This image was taken at an angle · the arm and leg are involved:
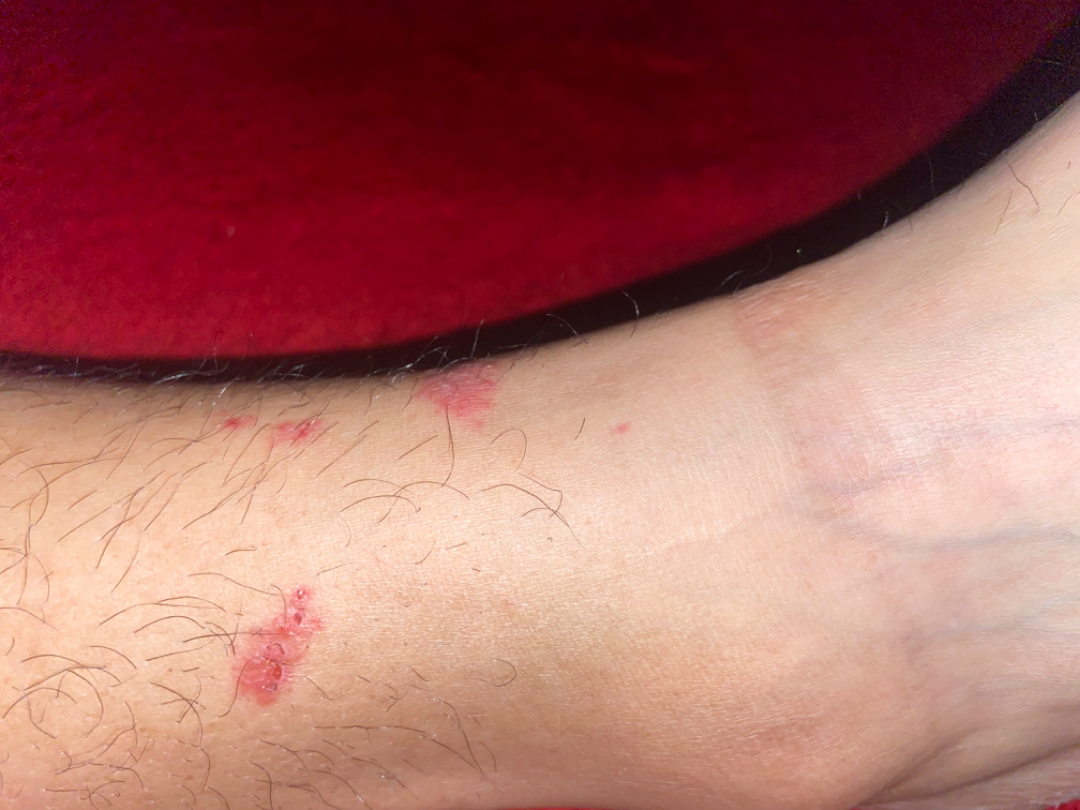| field | value |
|---|---|
| assessment | indeterminate |
| present for | less than one week |
| patient describes the issue as | a rash |
| texture | fluid-filled |
| reported symptoms | itching |
| constitutional symptoms | none reported |